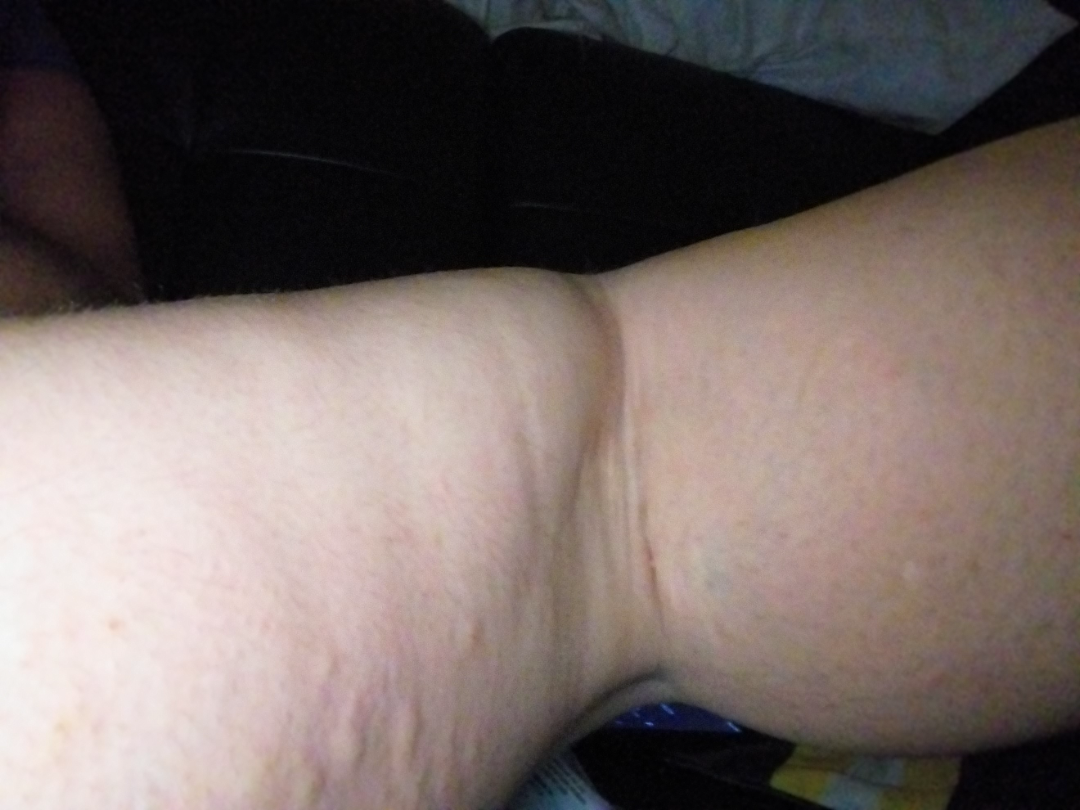The photo was captured at a distance.
The lesion involves the leg.
The patient is a female aged 40–49.
The reviewing dermatologists' impression was: Urticaria (50%); Allergic Contact Dermatitis (50%).